A dermoscopic image of a skin lesion.
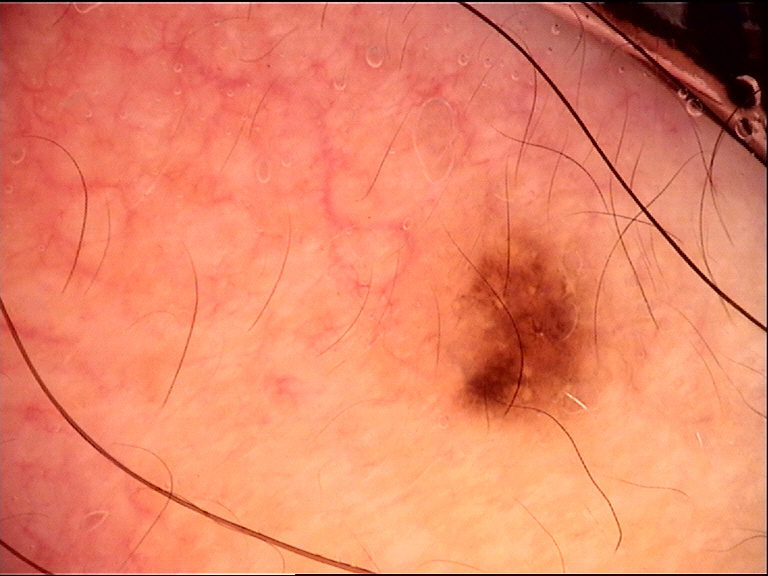{"diagnosis": {"name": "dysplastic junctional nevus", "code": "jd", "malignancy": "benign", "super_class": "melanocytic", "confirmation": "expert consensus"}}